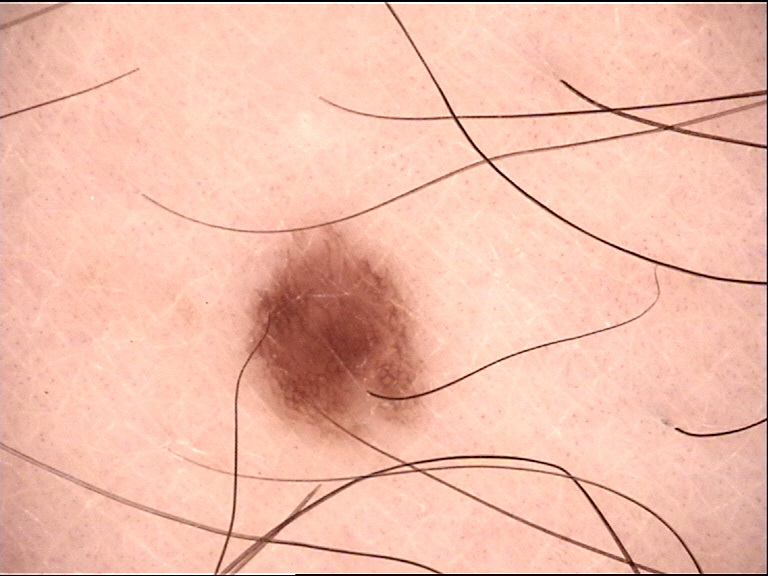A dermoscopic photograph of a skin lesion. Consistent with a benign lesion — a dysplastic junctional nevus.